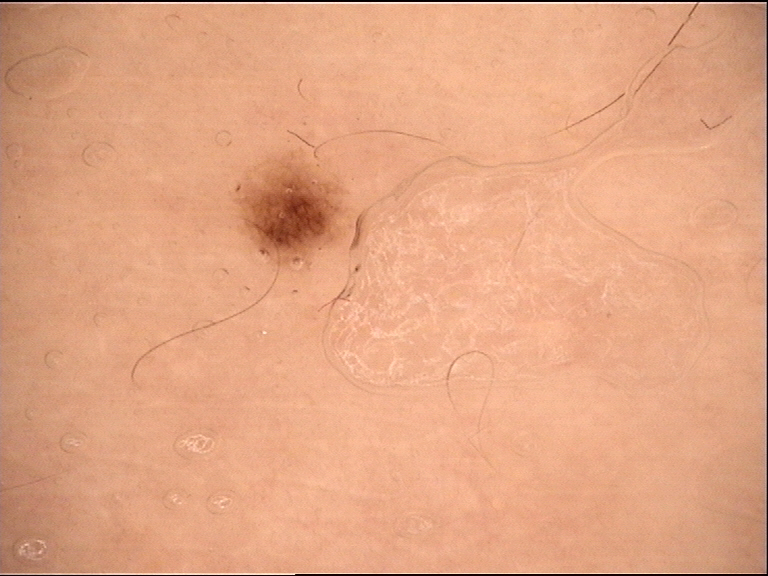| key | value |
|---|---|
| modality | dermatoscopy |
| label | dysplastic junctional nevus (expert consensus) |